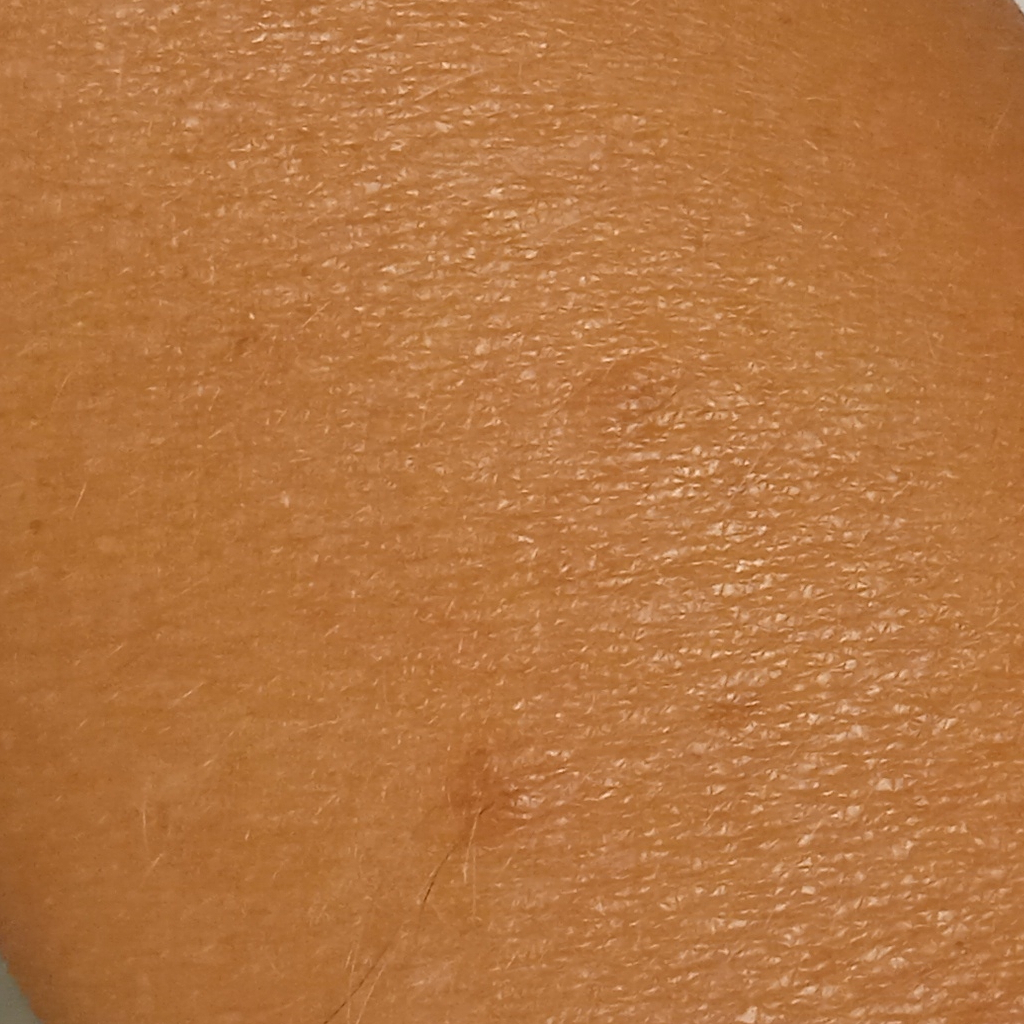The reviewing dermatologists could not reach a confident diagnosis. {"referral": "research study (no referral diagnosis)", "mole_burden": "a moderate number of melanocytic nevi", "risk_factors": {"positive": ["a history of sunbed use"]}, "sun_reaction": "skin tans without first burning", "image": "clinical photograph"}